A dermatoscopic image of a skin lesion.
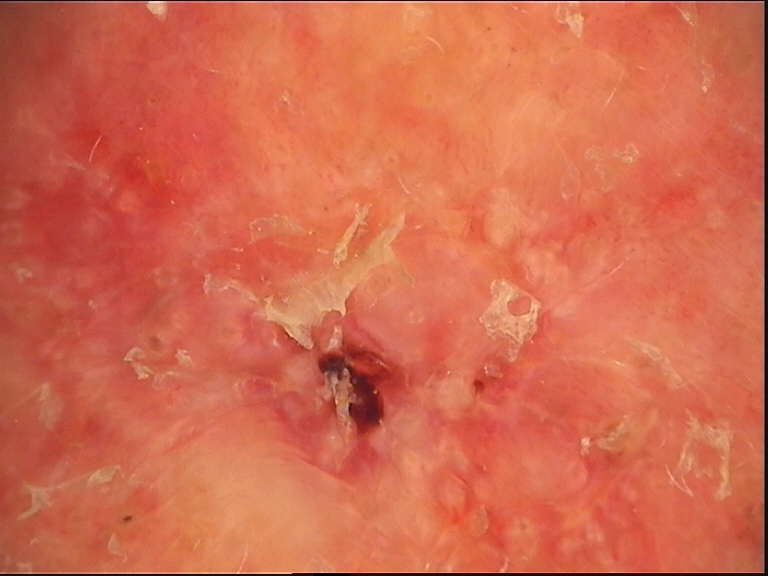Histopathology confirmed a skin cancer — a basal cell carcinoma.